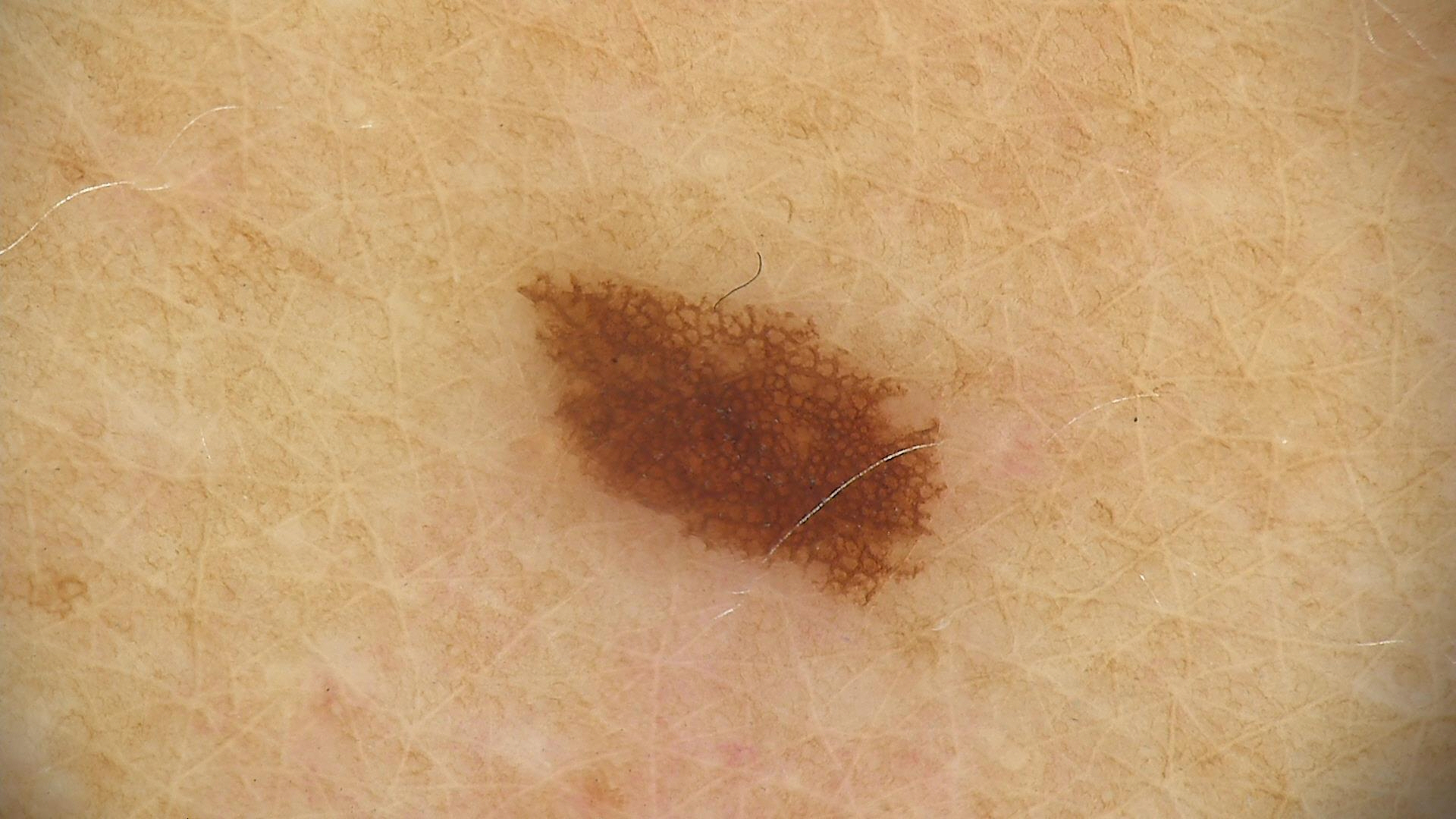Q: What kind of image is this?
A: dermoscopy
Q: What is the diagnosis?
A: dysplastic junctional nevus (expert consensus)